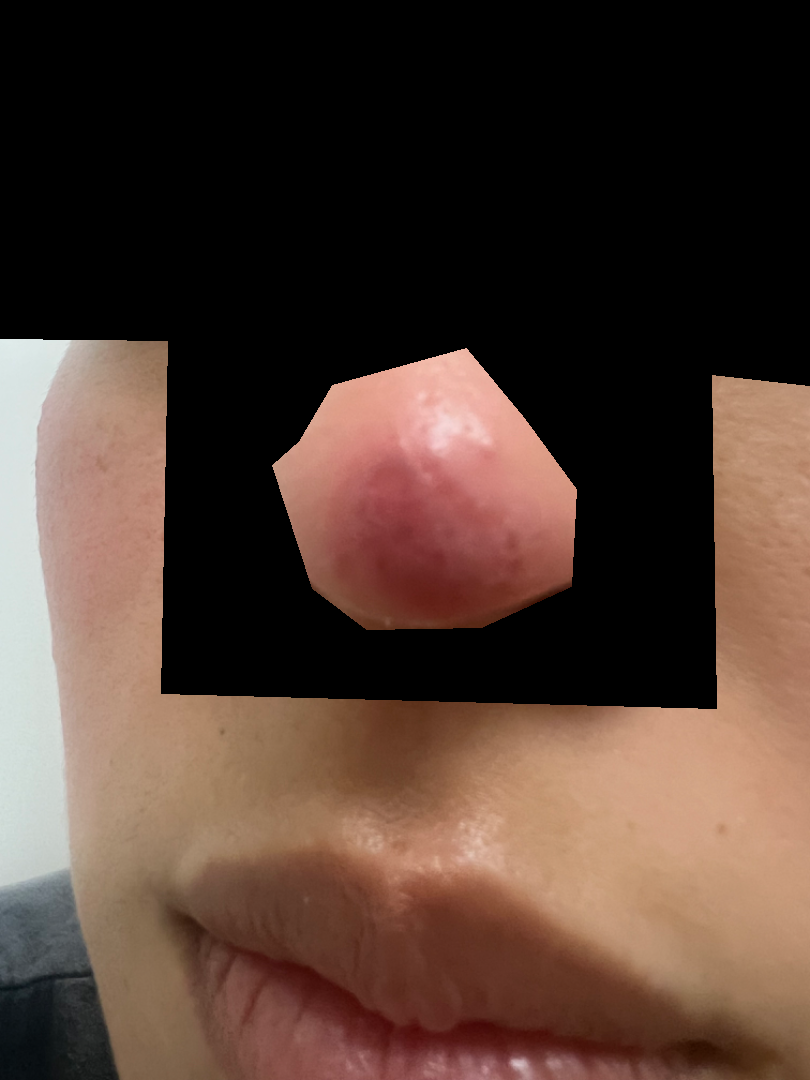– assessment: not assessable
– present for: less than one week
– contributor: female, age 18–29
– patient describes the issue as: skin that appeared healthy to them
– view: at a distance
– patient-reported symptoms: bothersome appearance